An image taken at an angle; the lesion involves the back of the hand — 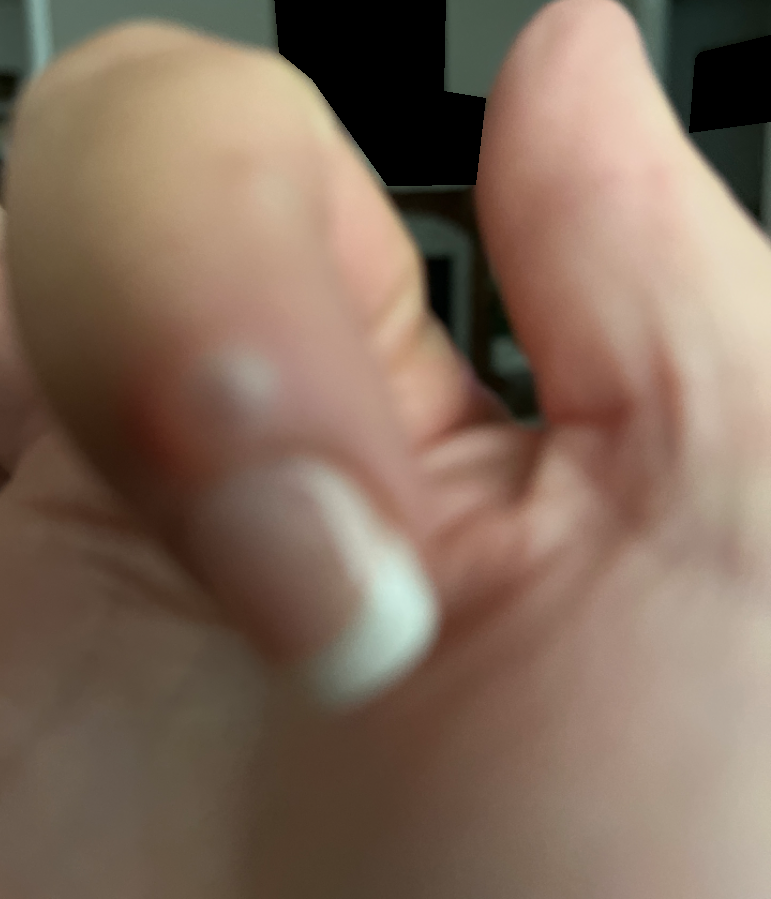assessment: indeterminate, systemic symptoms: none reported, patient describes the issue as: a growth or mole, symptom duration: one to three months, symptoms: bothersome appearance and enlargement, skin tone: human graders estimated MST 3 (US pool) or 2 (India pool), texture: raised or bumpy.